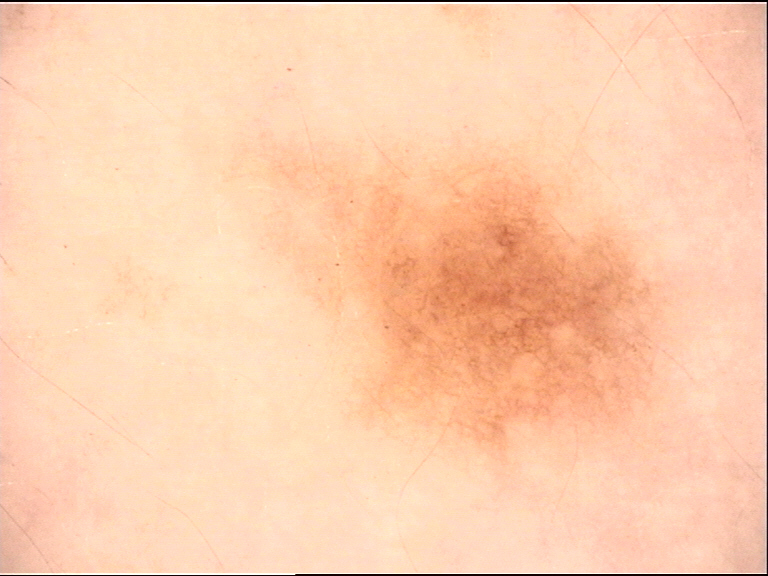Labeled as a junctional nevus.